A dermoscopy image of a single skin lesion.
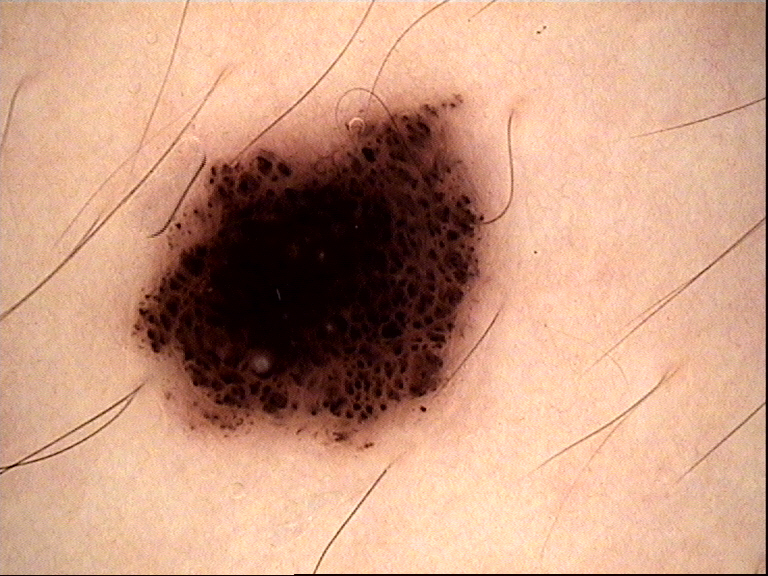The diagnosis was a banal lesion — a compound nevus.